A dermoscopic close-up of a skin lesion:
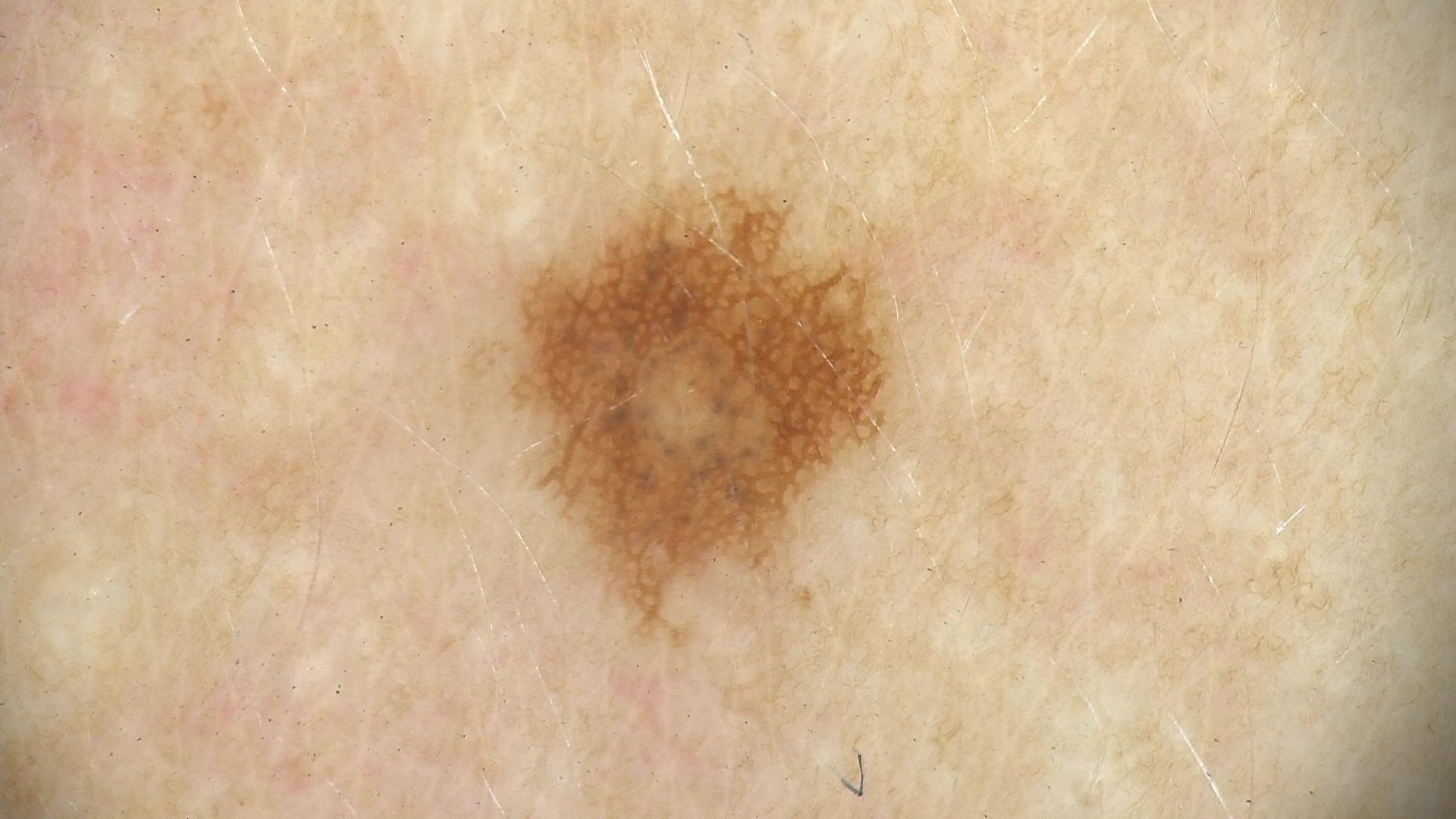Consistent with a benign lesion — a dysplastic compound nevus.